A clinical photo of a skin lesion taken with a smartphone. A patient aged 39:
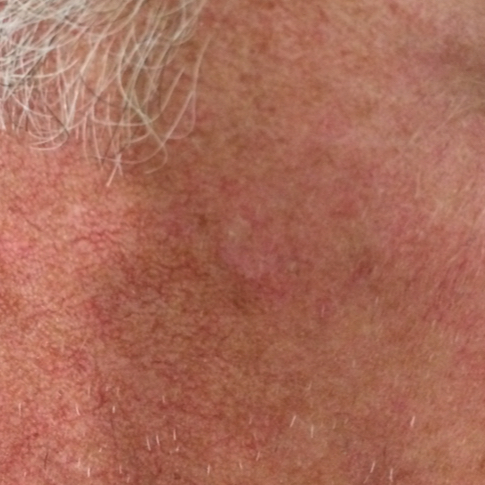Located on the face.
By the patient's account, the lesion does not itch and has not grown.
The consensus clinical diagnosis was a lesion with uncertain malignant potential — an actinic keratosis.